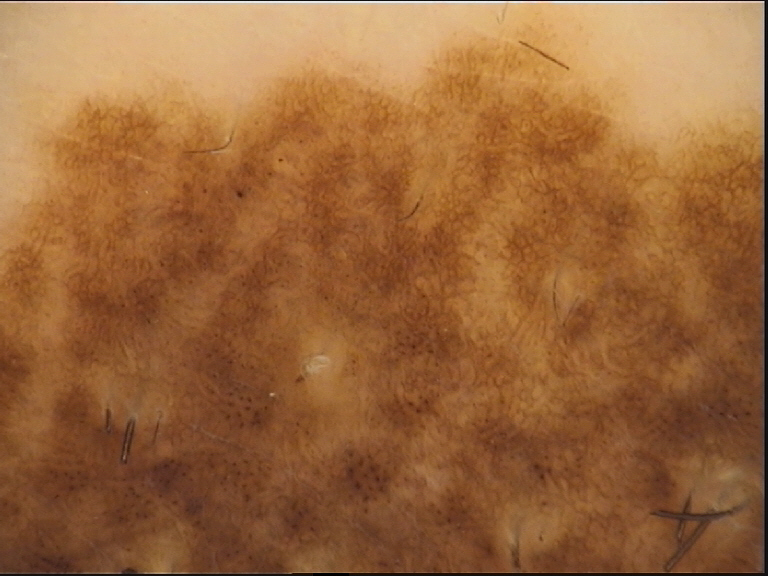Findings:
A dermoscopy image of a single skin lesion. The architecture is that of a banal lesion.
Conclusion:
Labeled as a congenital compound nevus.